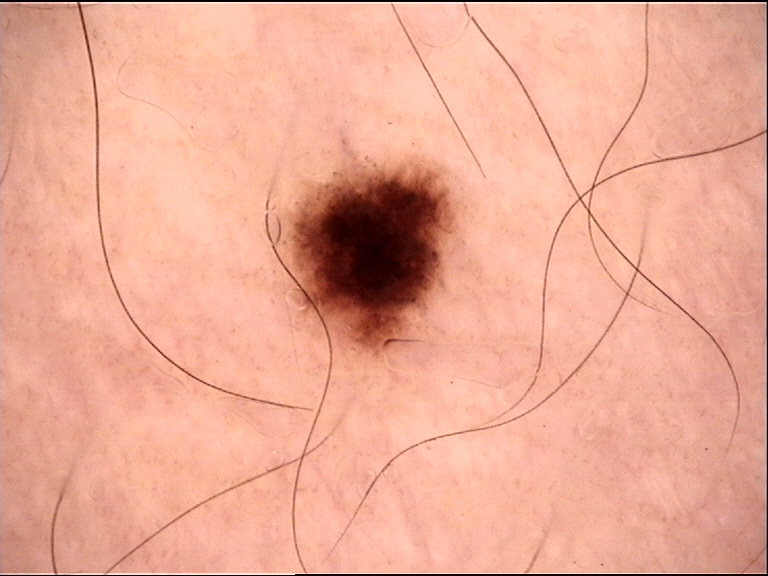diagnosis=junctional nevus (expert consensus)